Dermoscopy of a skin lesion:
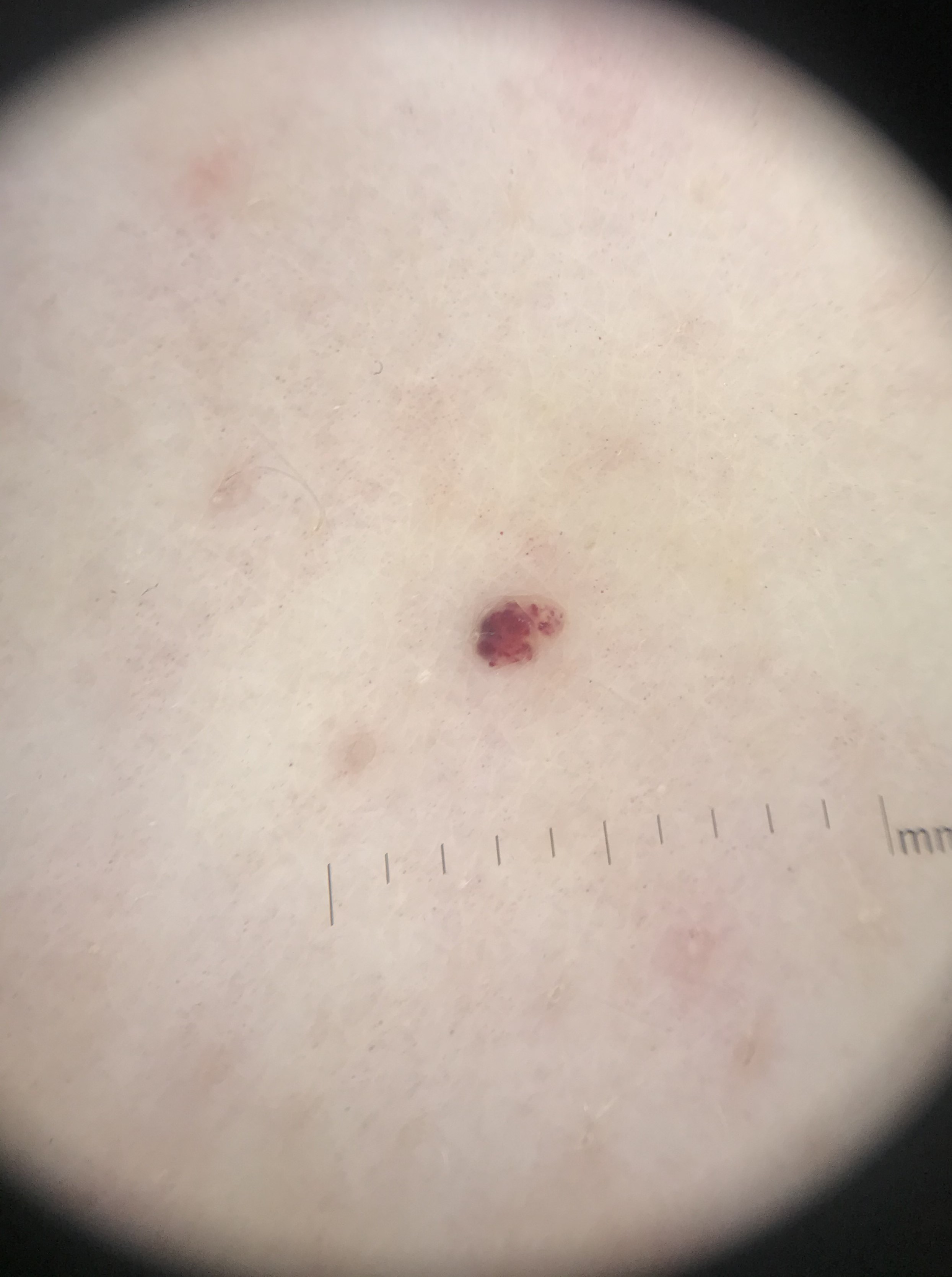The morphology is that of a vascular lesion. The diagnostic label was a hemangioma.